A dermoscopy image of a single skin lesion: 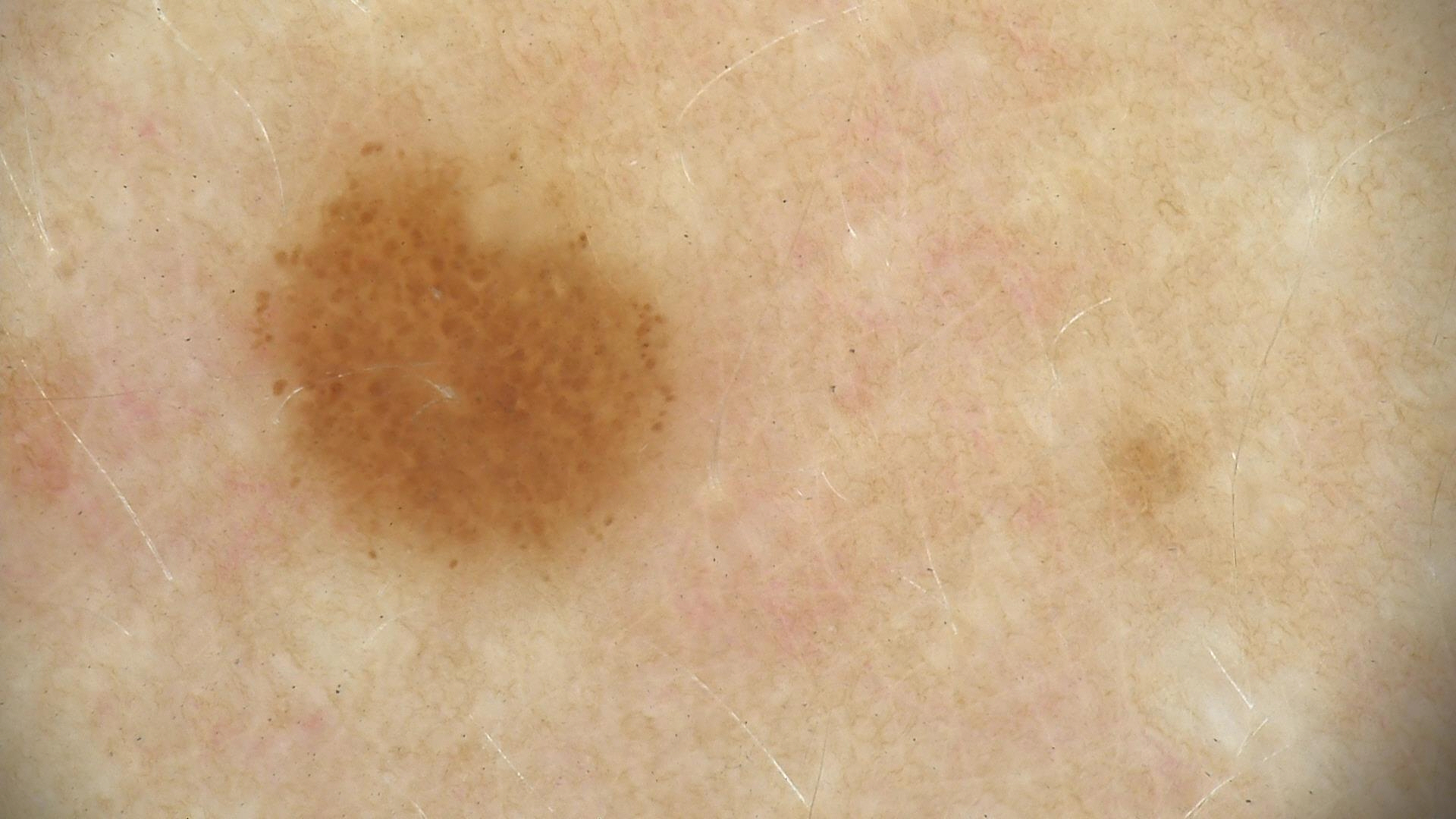The diagnosis was a dysplastic junctional nevus.